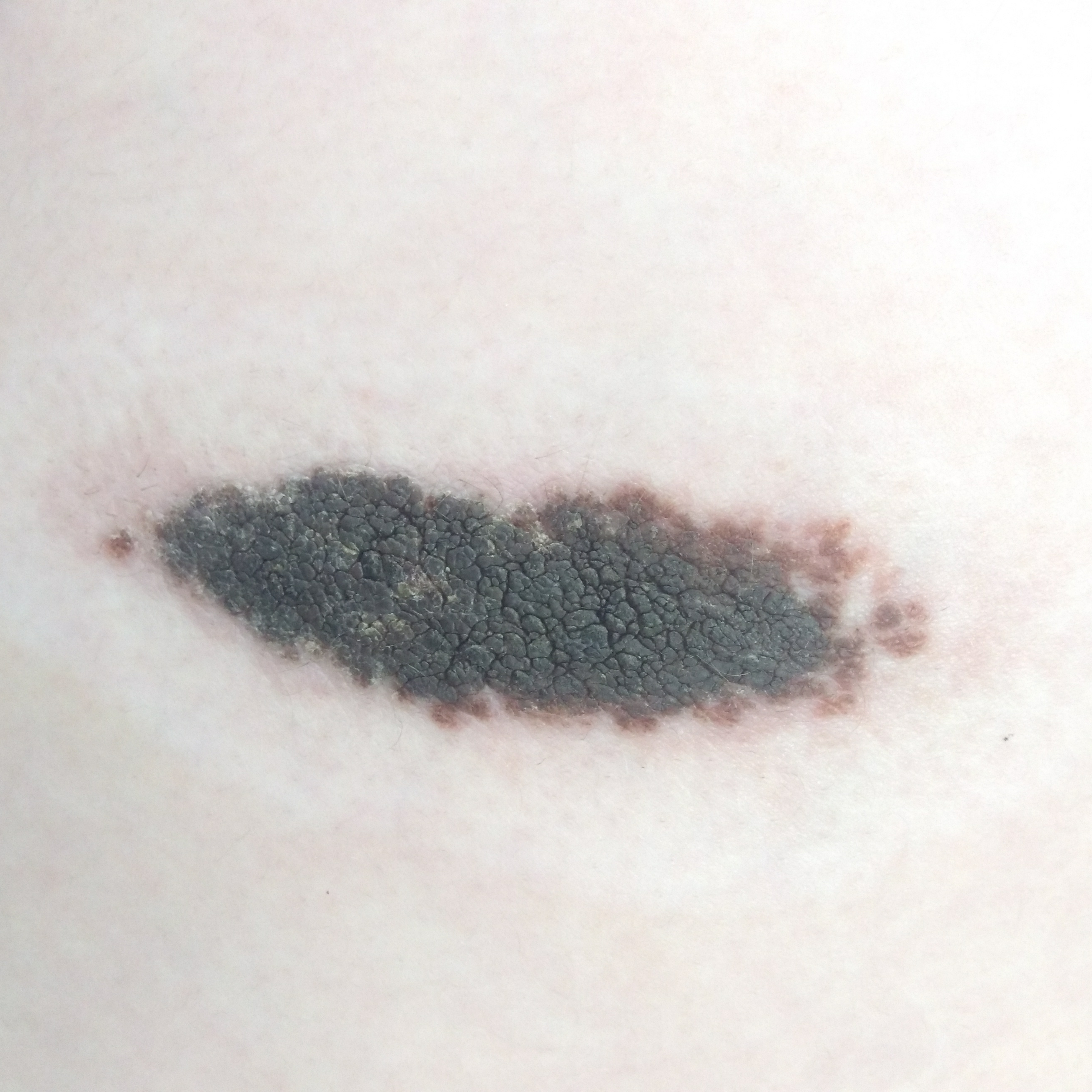Q: Skin phototype?
A: II
Q: How was this image acquired?
A: clinical photo
Q: Who is the patient?
A: female, 13 years old
Q: What is the anatomic site?
A: a thigh
Q: What are the lesion's dimensions?
A: 89x27 mm
Q: What symptoms does the patient report?
A: elevation
Q: What did the workup show?
A: nevus (biopsy-proven)